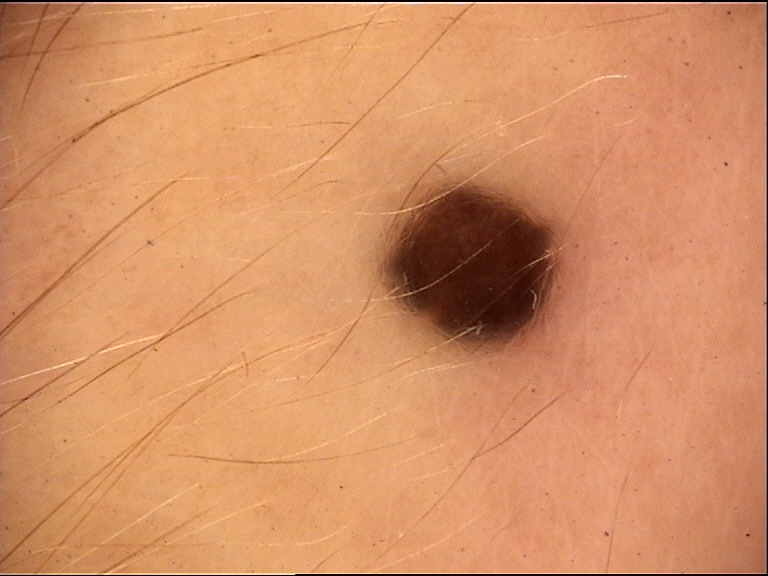label = blue nevus (expert consensus).